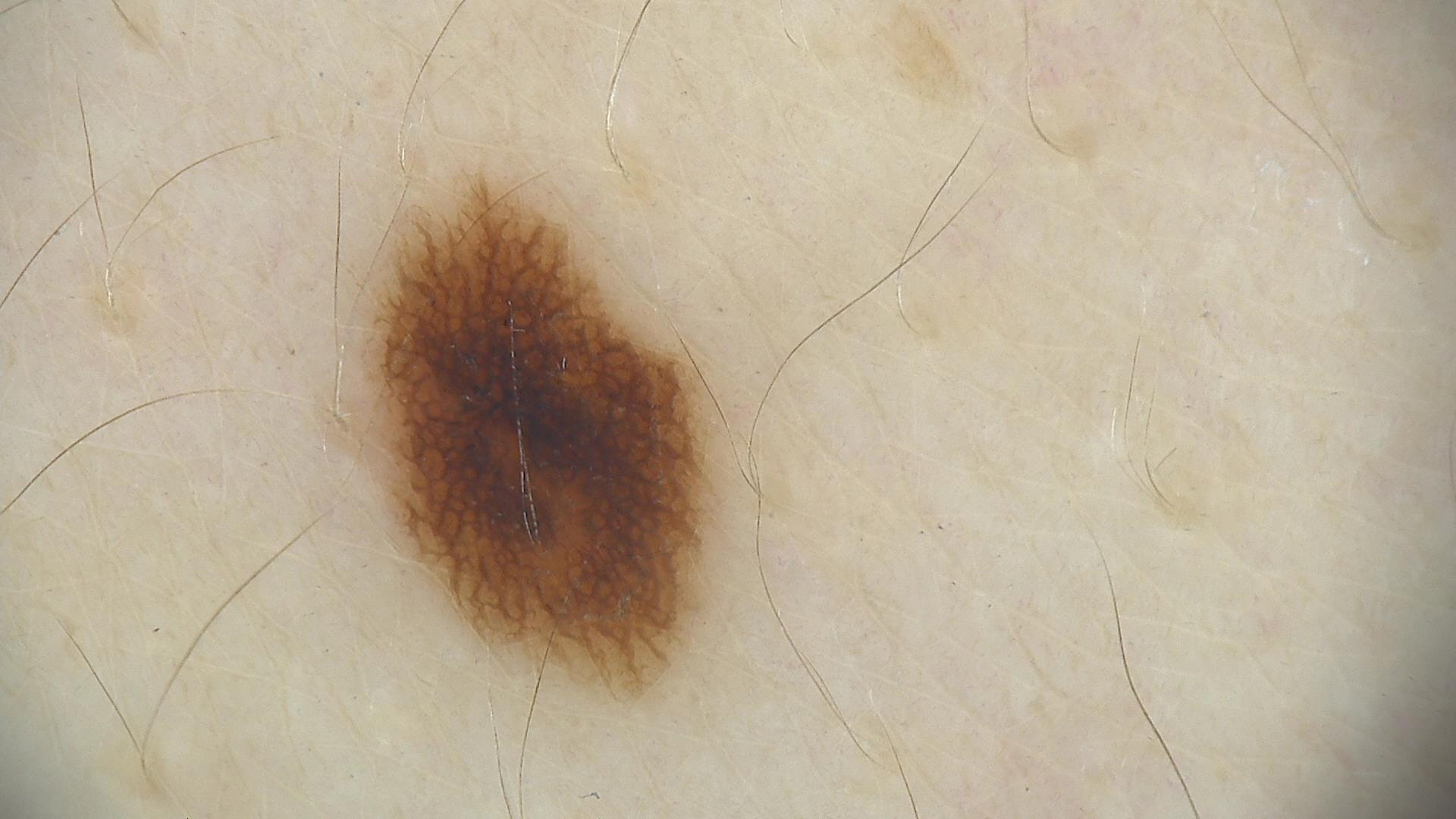A dermoscopic close-up of a skin lesion. Diagnosed as a benign lesion — a dysplastic junctional nevus.